Located on the front of the torso. Close-up view — 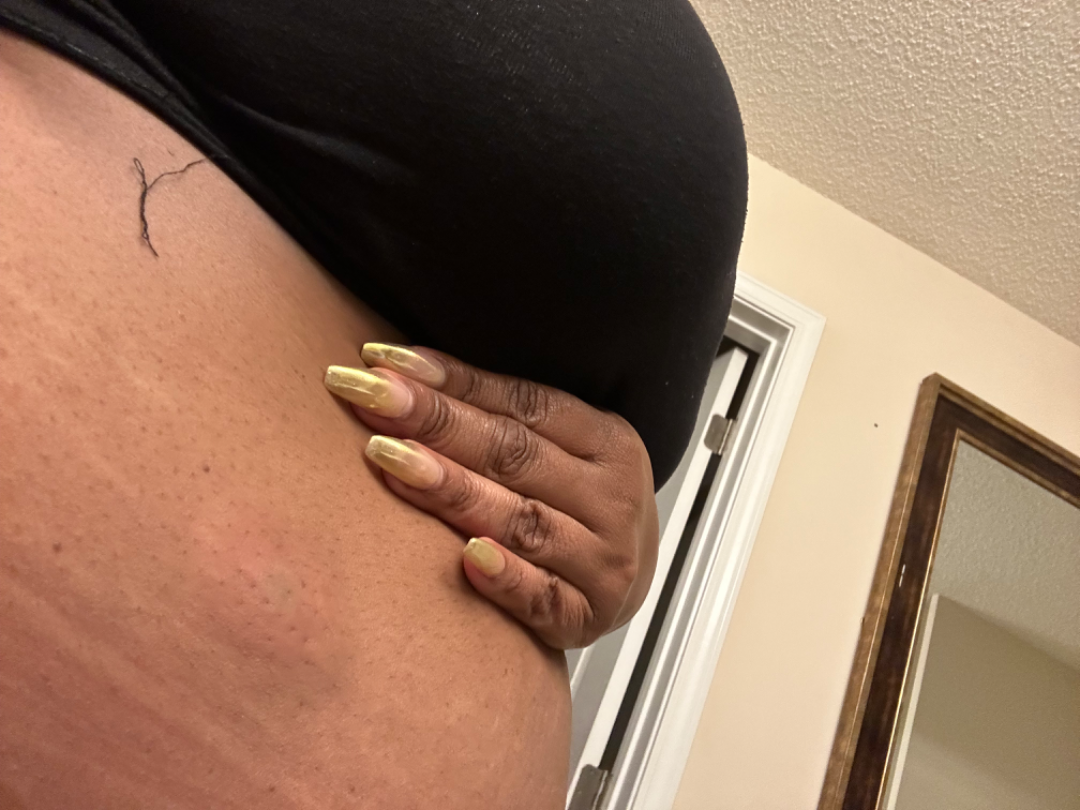Case summary:
- impression: the leading consideration is Insect Bite; also raised was Geographic tongue; less likely is Urticaria